The photograph is a close-up of the affected area. Located on the top or side of the foot, leg and arm.
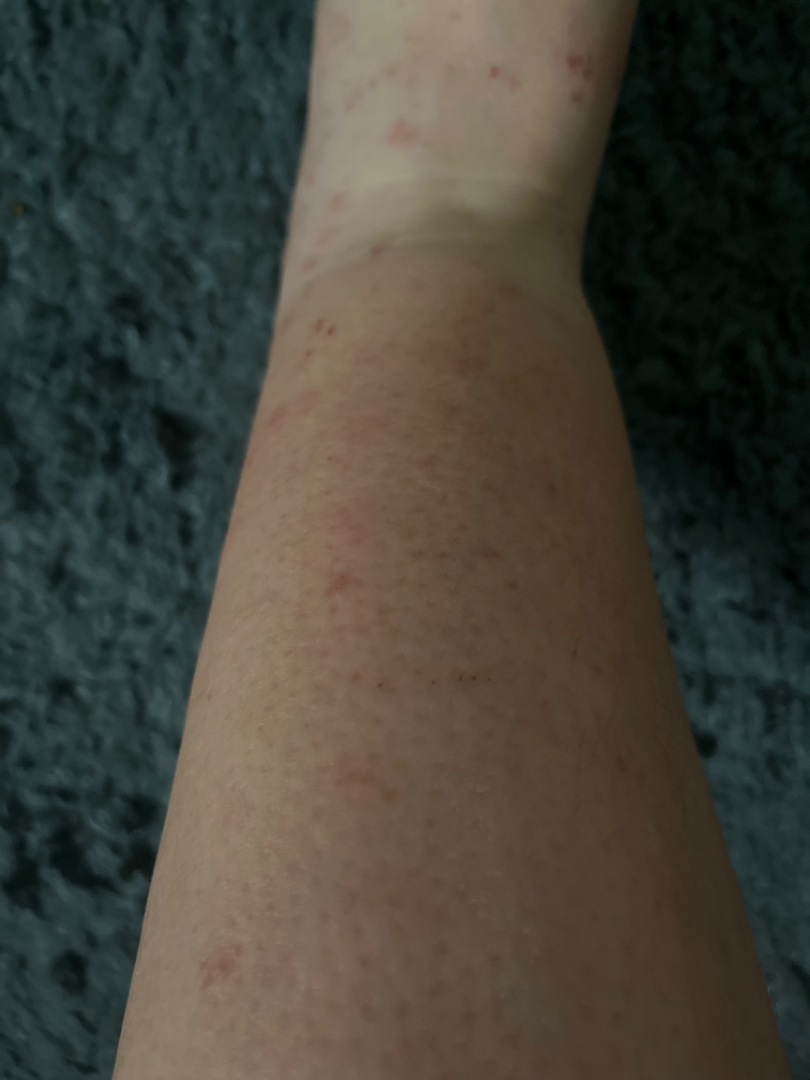<report>
  <assessment>indeterminate from the photograph</assessment>
</report>